Located on the head or neck · the photograph is a close-up of the affected area:
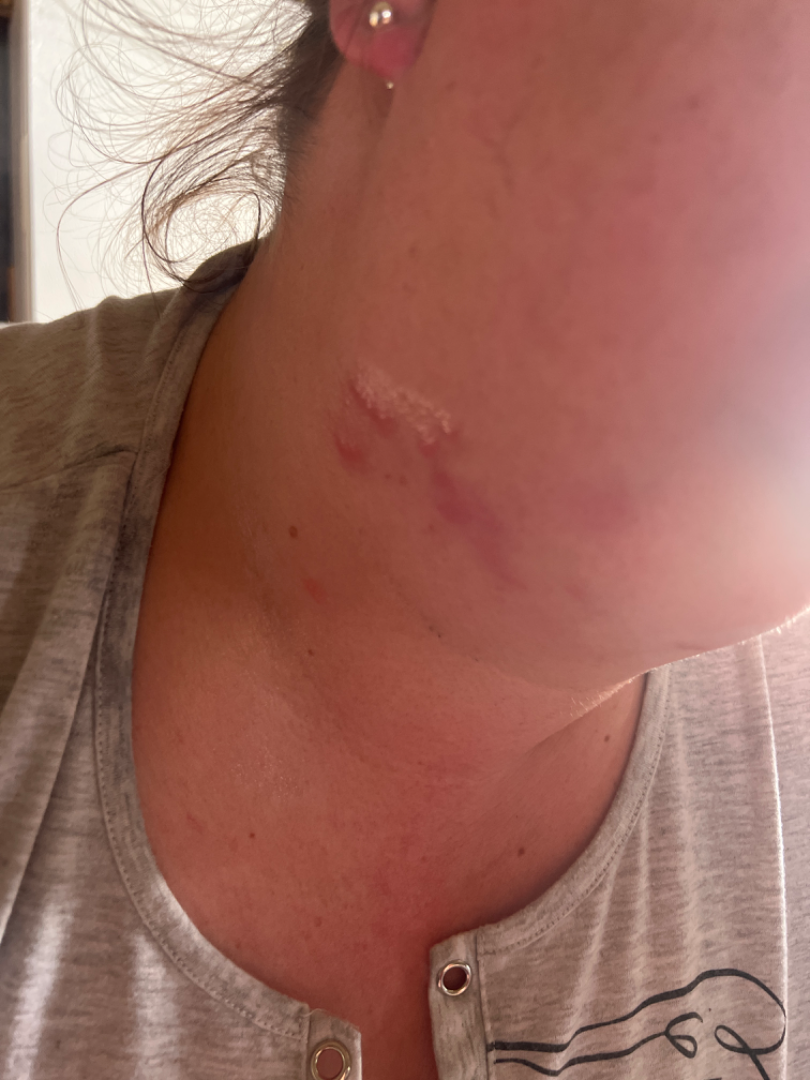  skin_tone:
    fitzpatrick: III
  duration: less than one week
  differential:
    leading:
      - Psoriasis